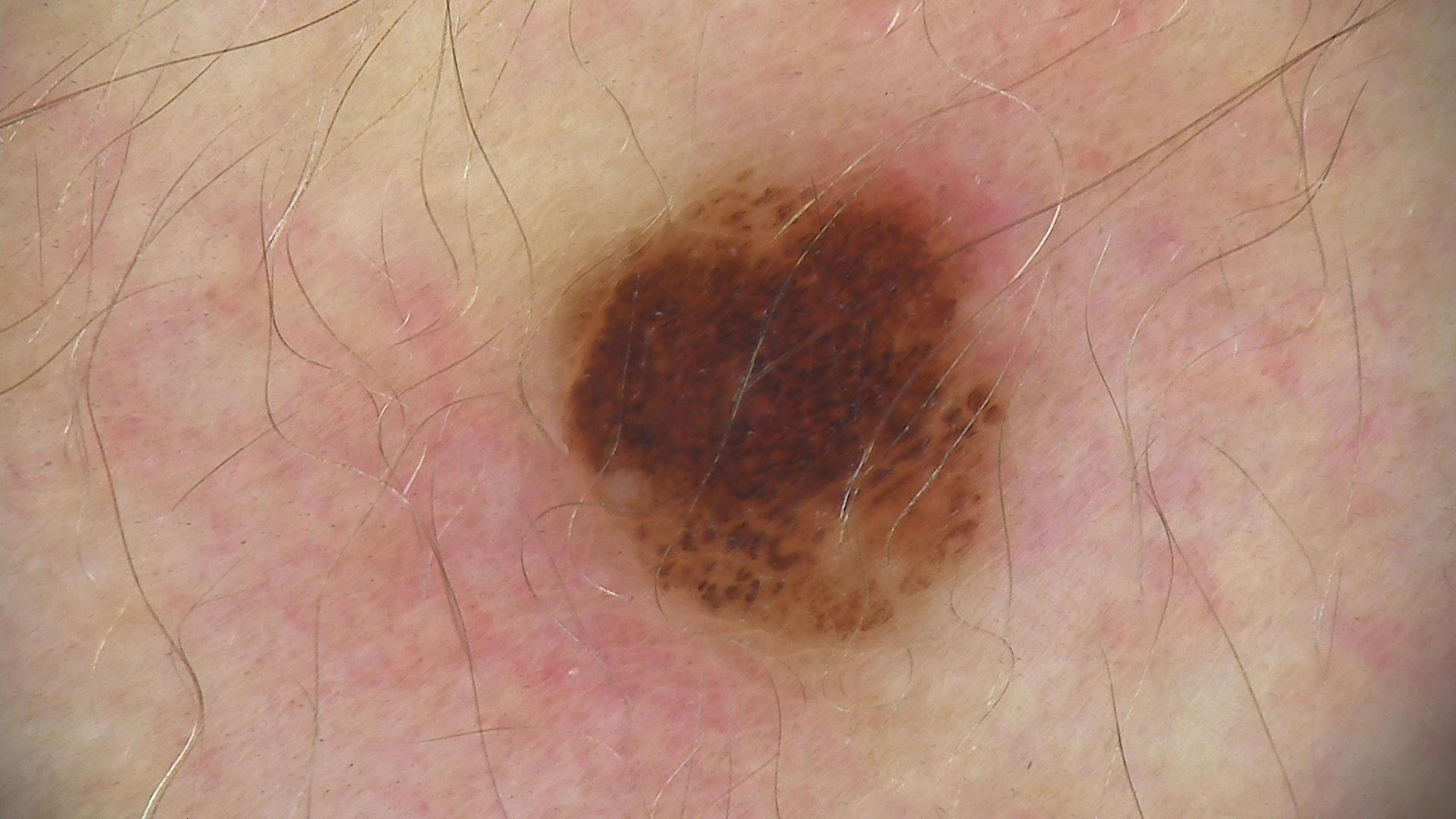{"diagnosis": {"name": "compound nevus", "code": "cb", "malignancy": "benign", "super_class": "melanocytic", "confirmation": "expert consensus"}}